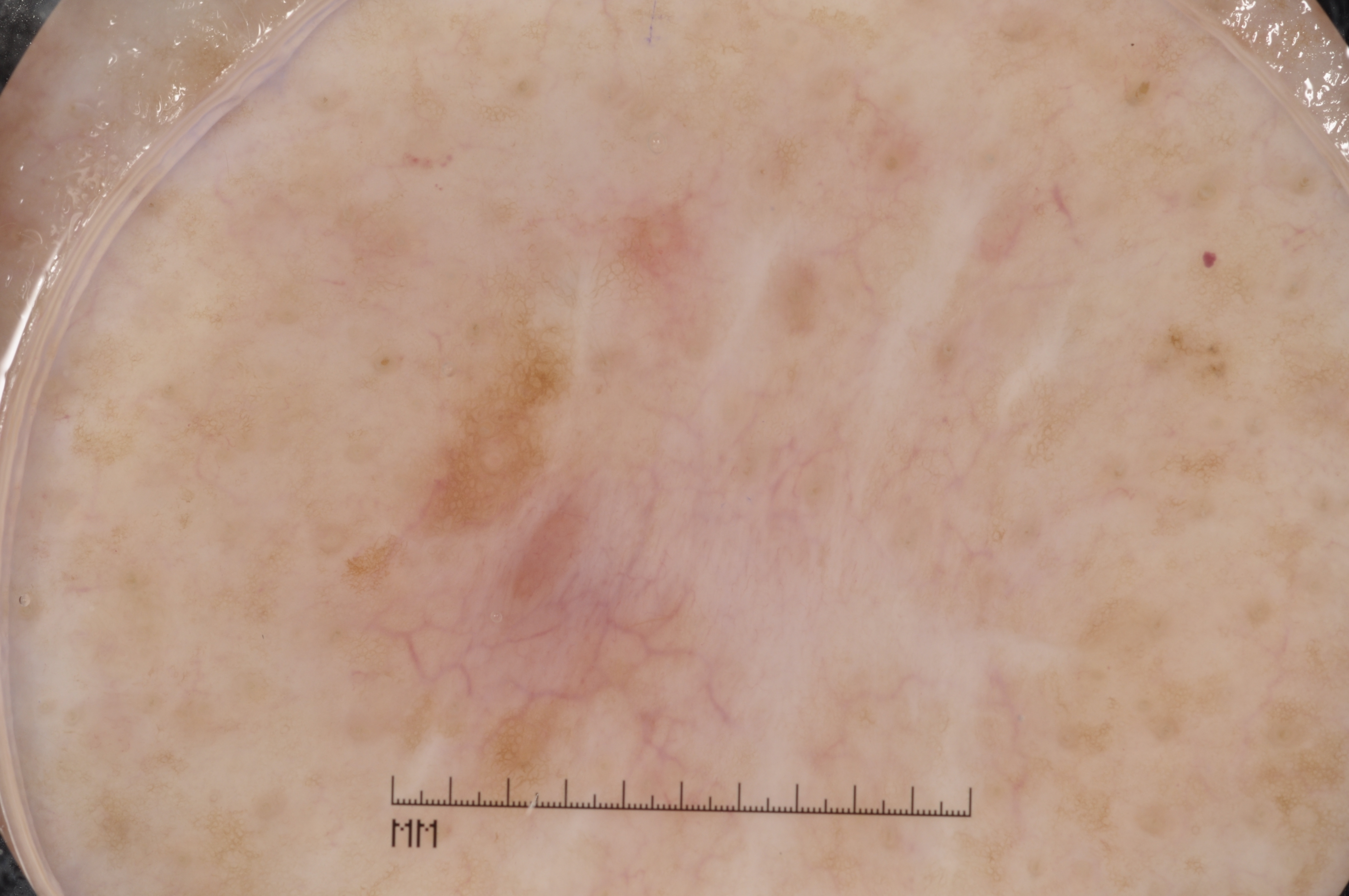A male patient, aged around 60. A dermoscopic view of a skin lesion. Dermoscopic assessment notes pigment network. With coordinates (x1, y1, x2, y2), the lesion occupies the region 318 183 740 821. Diagnosed as a melanocytic nevus.